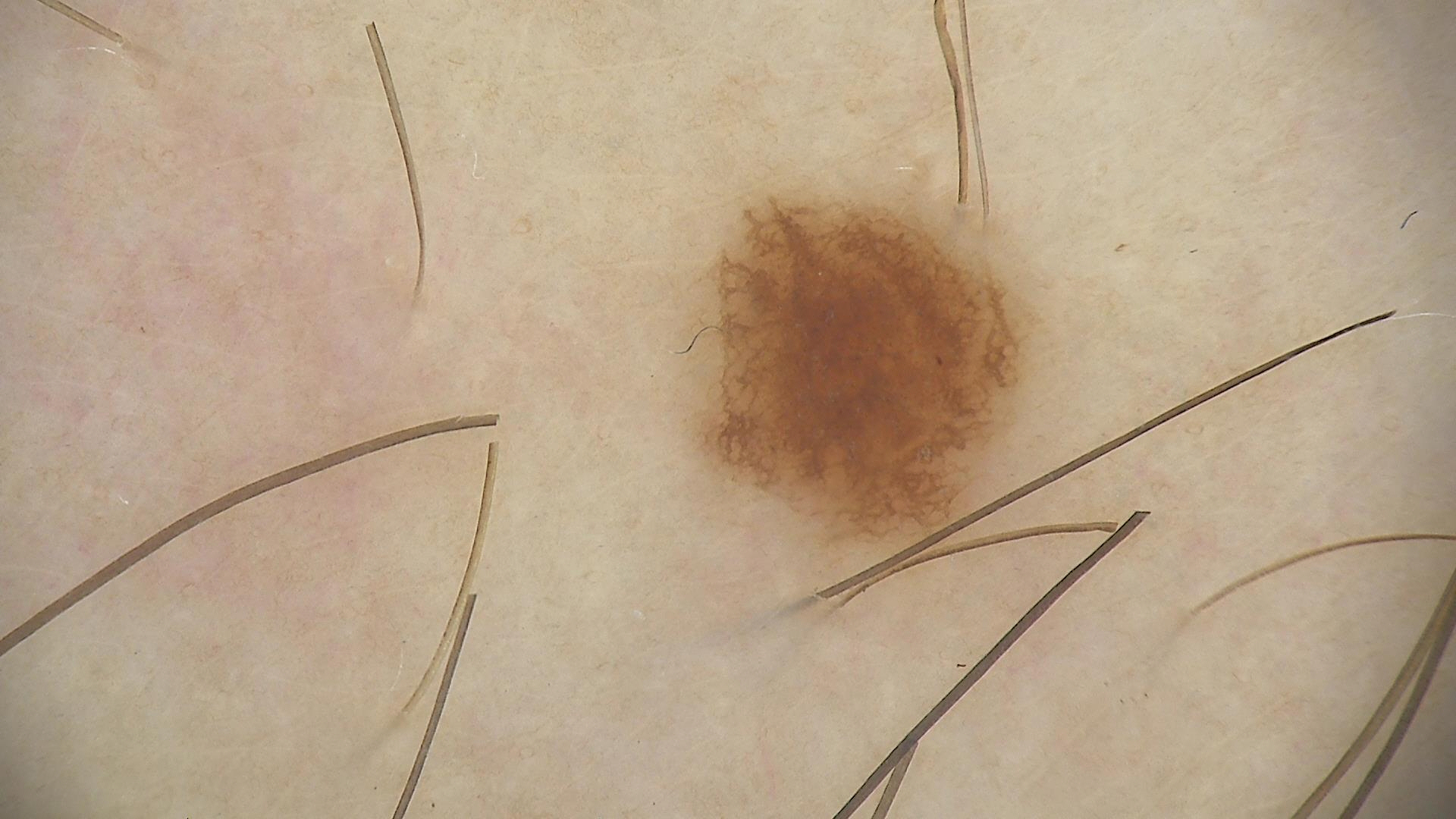A dermatoscopic image of a skin lesion.
The morphology is that of a banal lesion.
Consistent with a junctional nevus.